The patient is a male aged approximately 85 or older · a dermatoscopic image of a skin lesion: 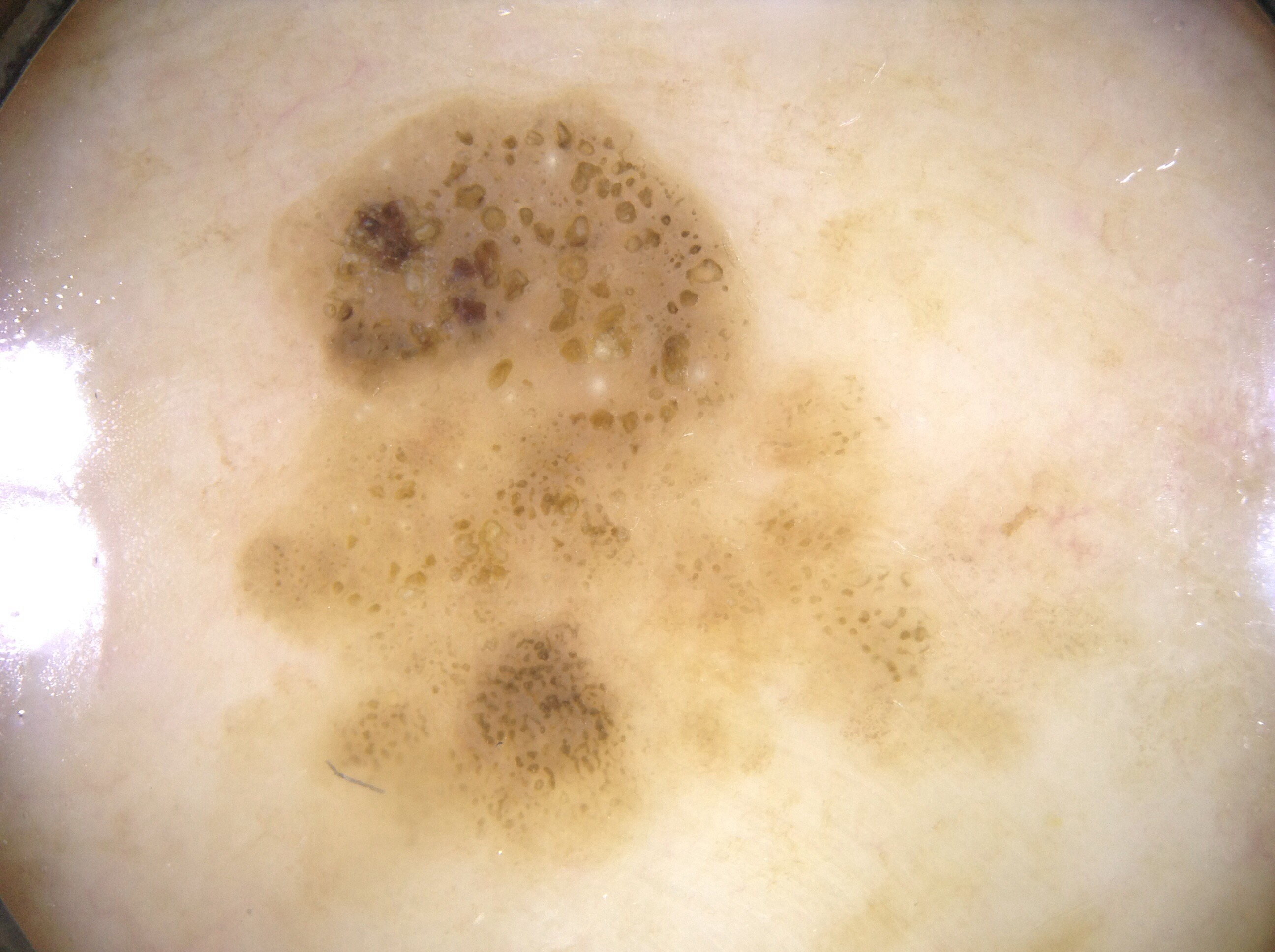location: bbox(212, 69, 1147, 915) | lesion size: ~41% of the field | features: milia-like cysts | assessment: a seborrheic keratosis, a non-melanocytic (keratinocytic) lesion.